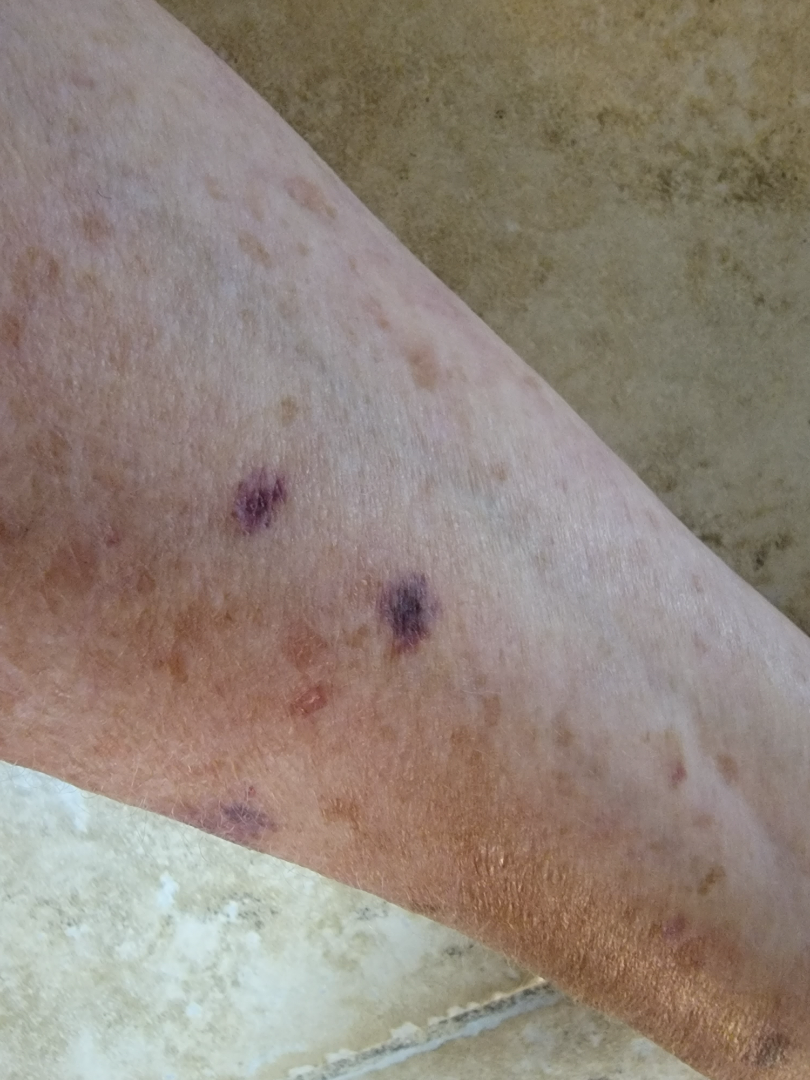{
  "shot_type": "close-up",
  "body_site": "arm",
  "differential": {
    "leading": [
      "ecchymoses"
    ]
  }
}